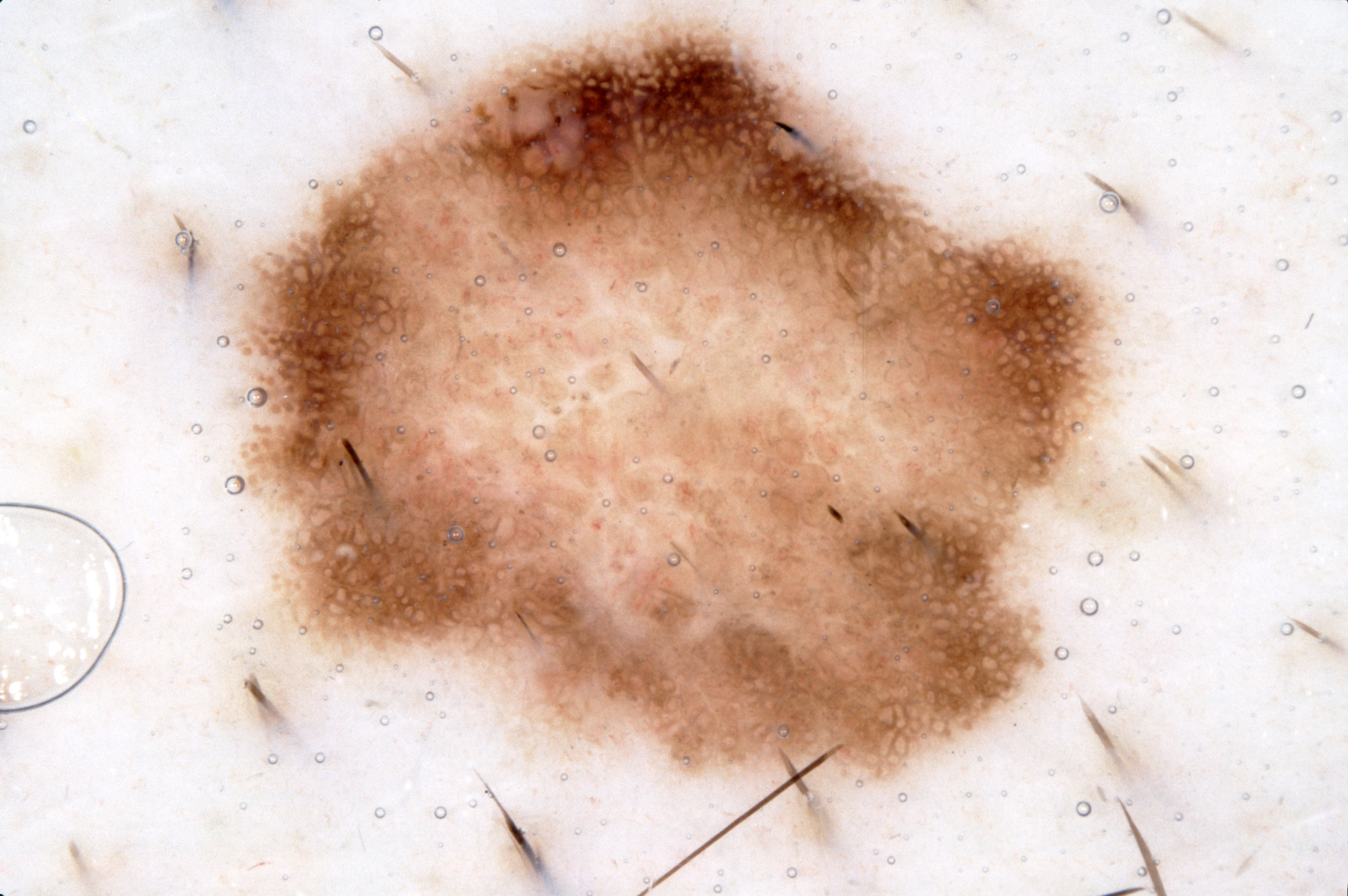  patient:
    sex: male
    age_approx: 45
  image:
    modality: dermoscopy
  lesion_location:
    bbox_xyxy:
      - 203
      - 4
      - 1143
      - 809
  dermoscopic_features:
    present:
      - milia-like cysts
      - negative network
      - pigment network
    absent:
      - streaks
  diagnosis:
    name: melanoma
    malignancy: malignant
    lineage: melanocytic
    provenance: histopathology